Skin tone: FST VI, a close-up photograph:
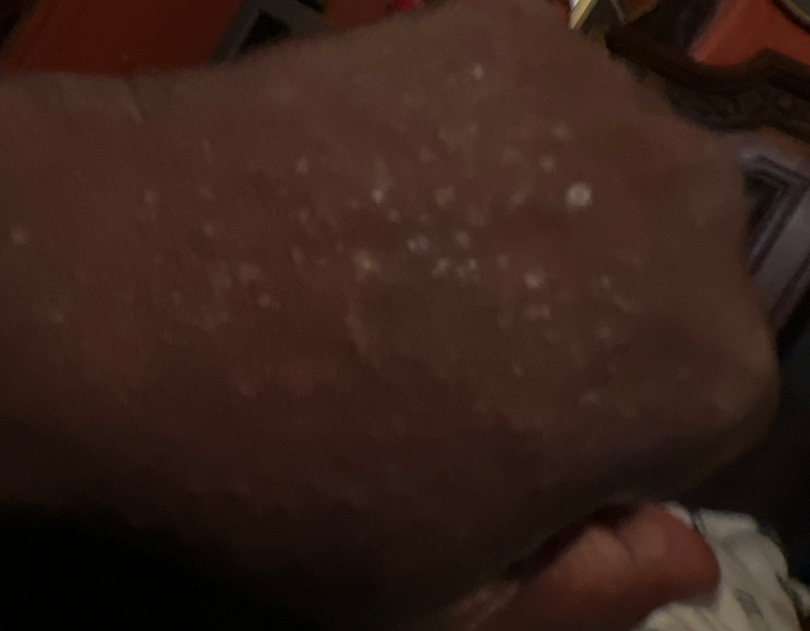Impression: The dermatologist could not determine a likely condition from the photograph alone.